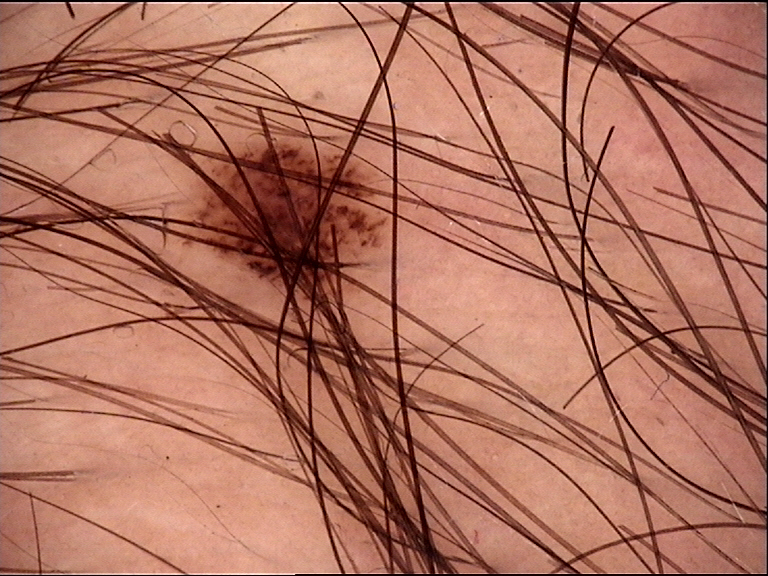diagnosis: dysplastic junctional nevus (expert consensus)